A dermoscopic image of a skin lesion.
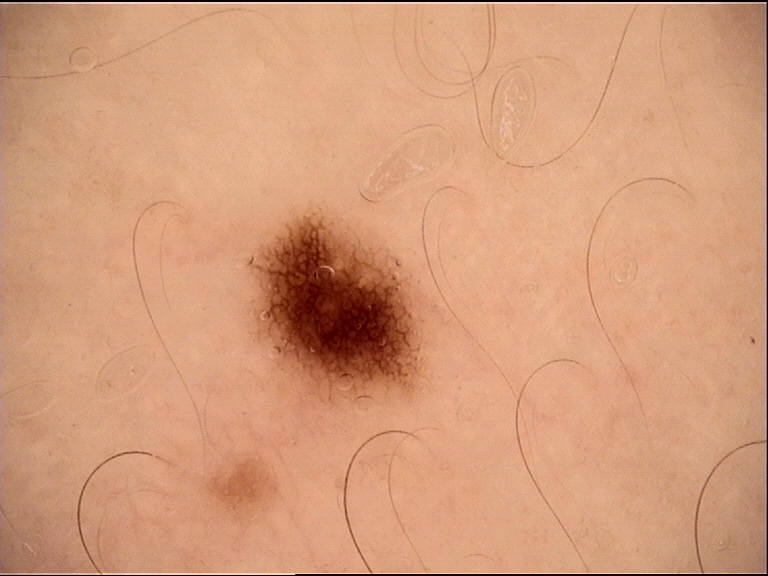Labeled as a dysplastic junctional nevus.